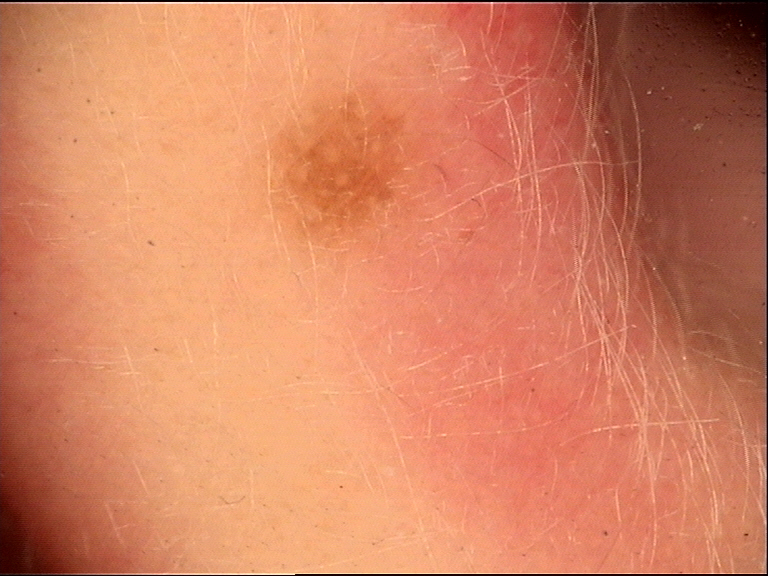image type: dermatoscopy; category: banal, compound; diagnosis: Miescher nevus (expert consensus).